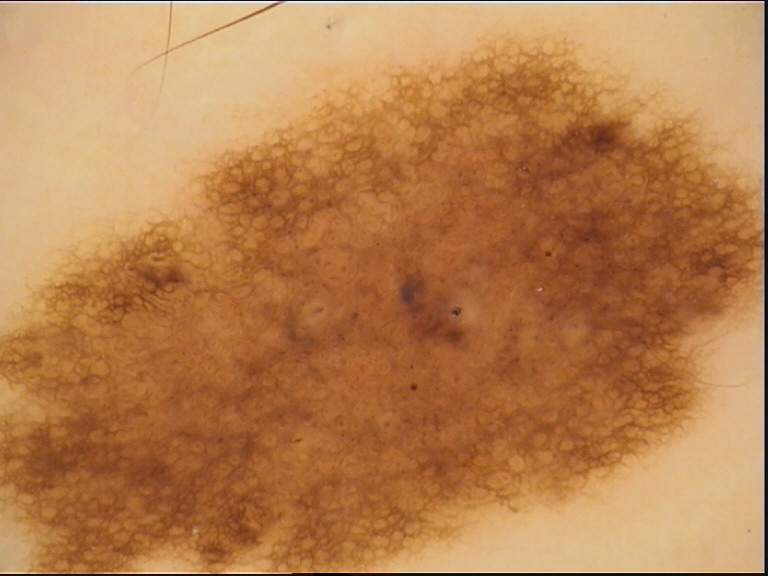A dermoscopic close-up of a skin lesion.
This is a banal lesion.
Diagnosed as a congenital junctional nevus.